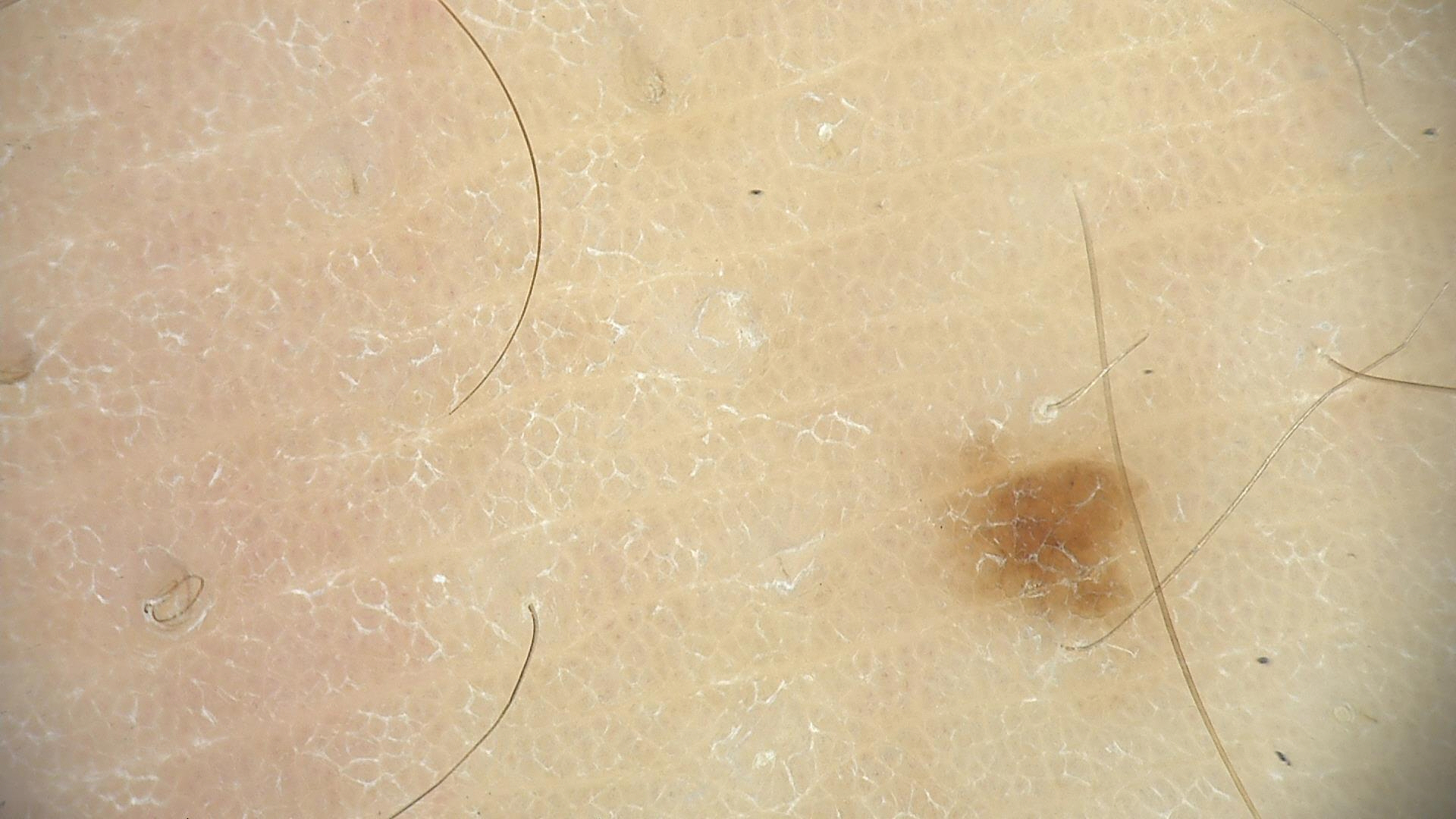modality — dermatoscopy; diagnosis — acral junctional nevus (expert consensus).